A skin lesion imaged with a dermatoscope.
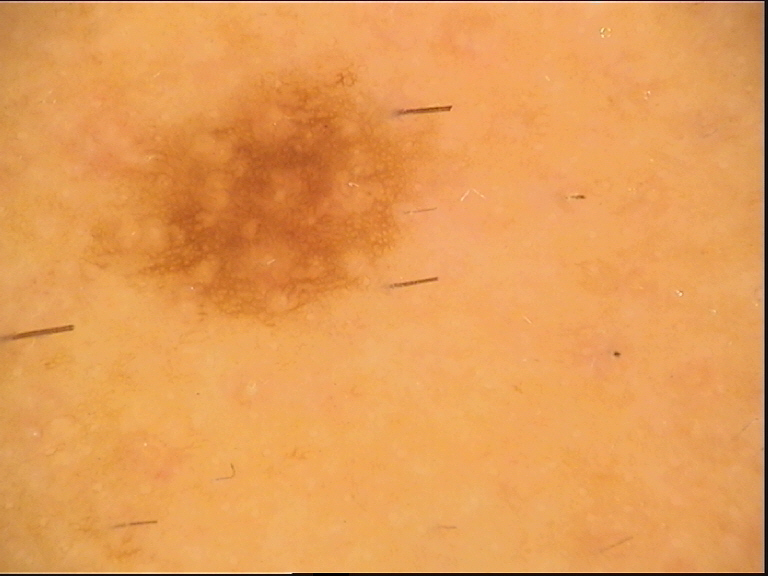Impression: The diagnostic label was a banal lesion — a junctional nevus.